A dermoscopic photograph of a skin lesion.
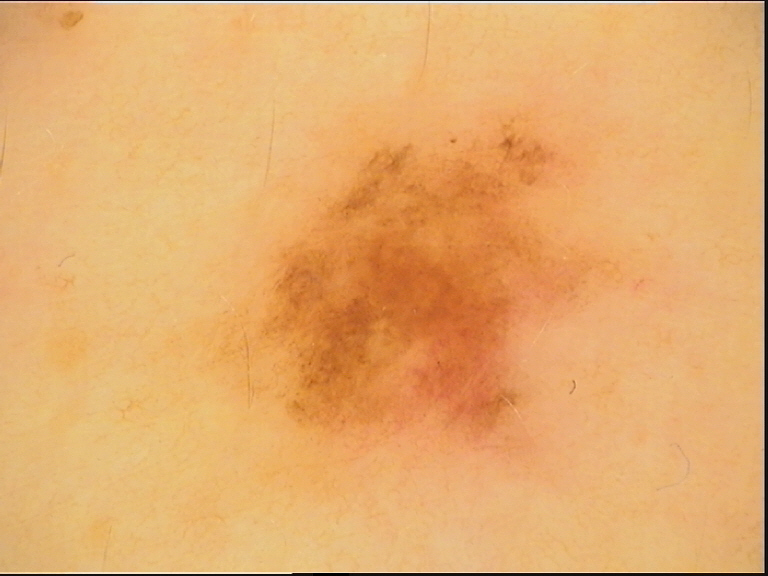Conclusion:
The diagnostic label was a benign lesion — a dysplastic junctional nevus.